A female patient aged 53 to 57 · a wide-field clinical photograph of a skin lesion · the patient was assessed as Fitzpatrick skin type III:
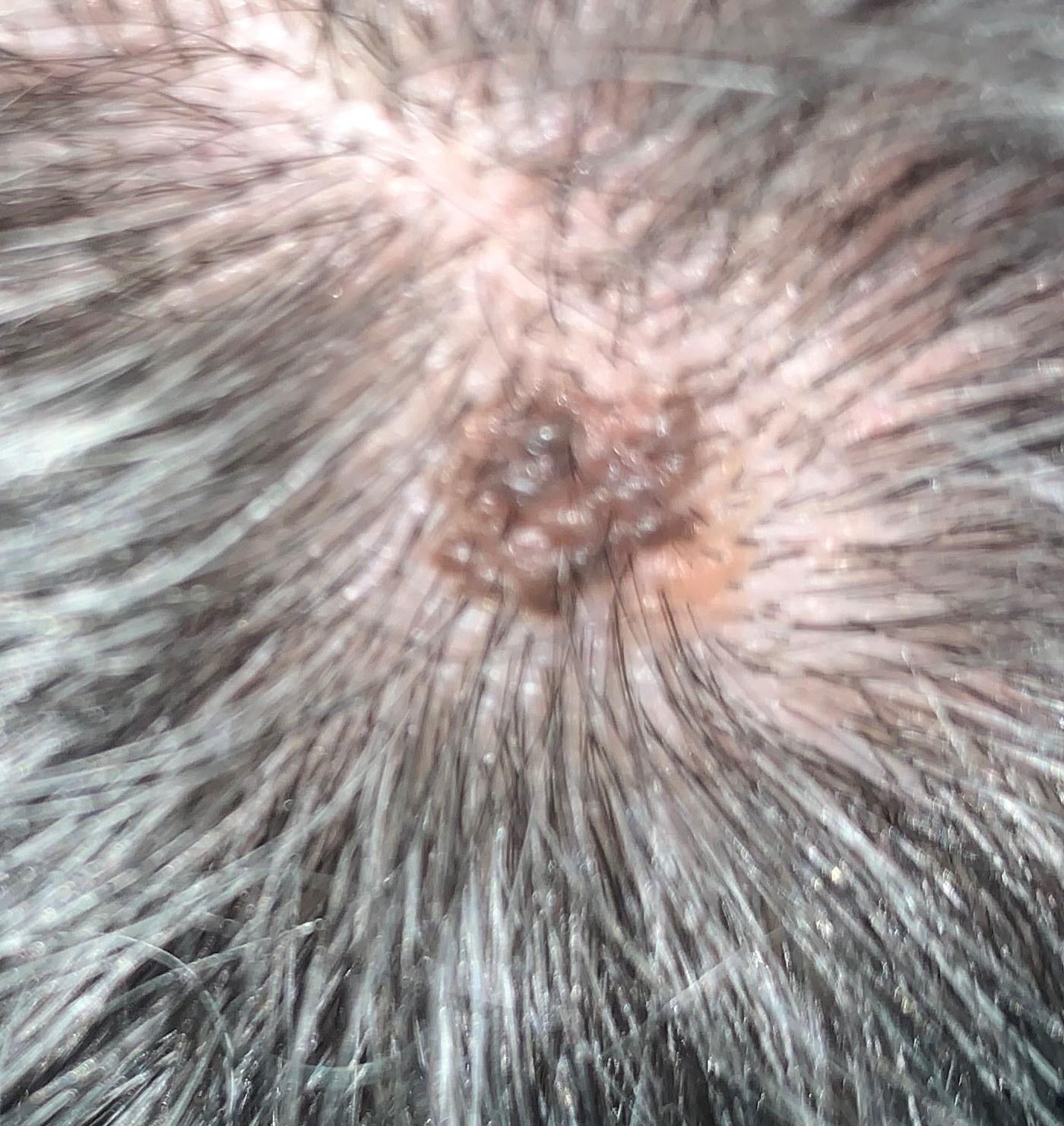Q: Where is the lesion located?
A: the head or neck
Q: What did the workup show?
A: Seborrheic keratosis (biopsy-proven)